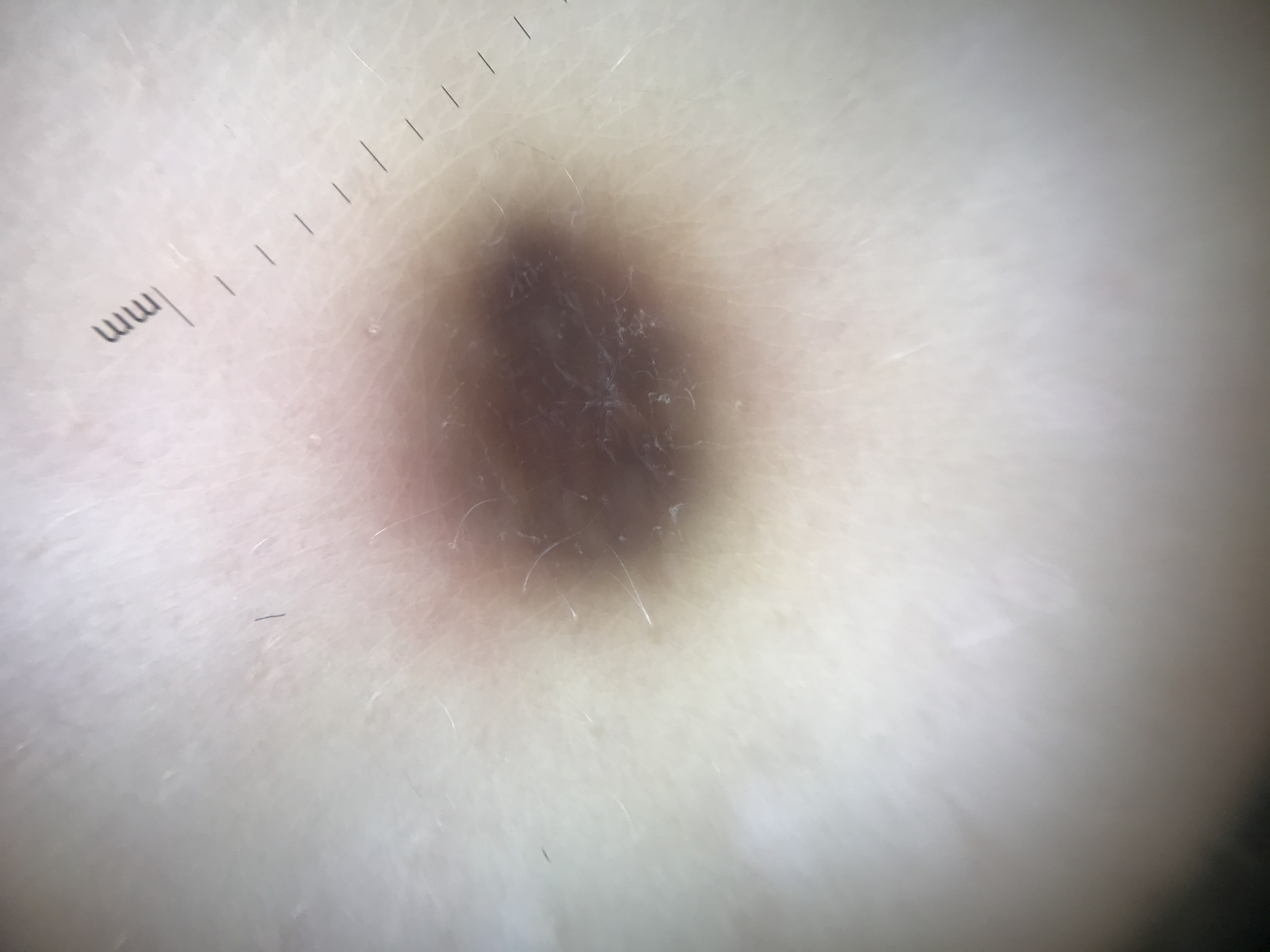{
  "image": "dermatoscopy",
  "diagnosis": {
    "name": "blue nevus",
    "code": "bdb",
    "malignancy": "benign",
    "super_class": "melanocytic",
    "confirmation": "expert consensus"
  }
}